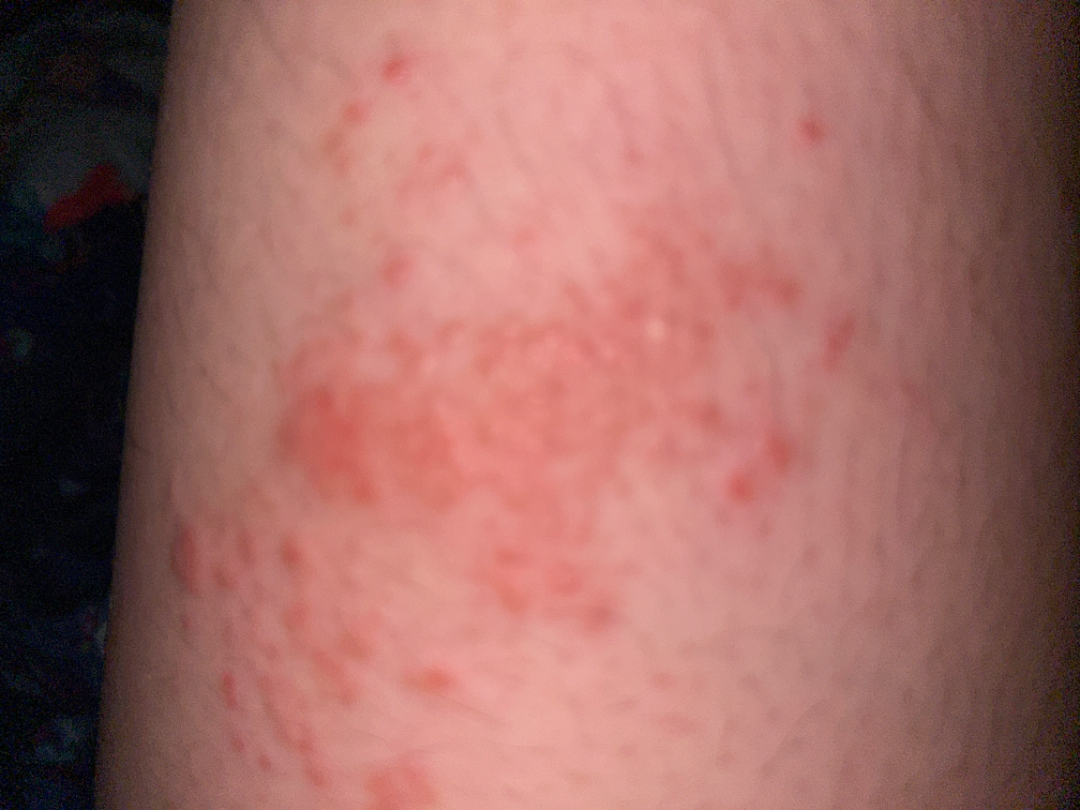Review: On teledermatology review, most likely Allergic Contact Dermatitis; possibly Tinea; also raised was Eczema.